This image was taken at an angle.
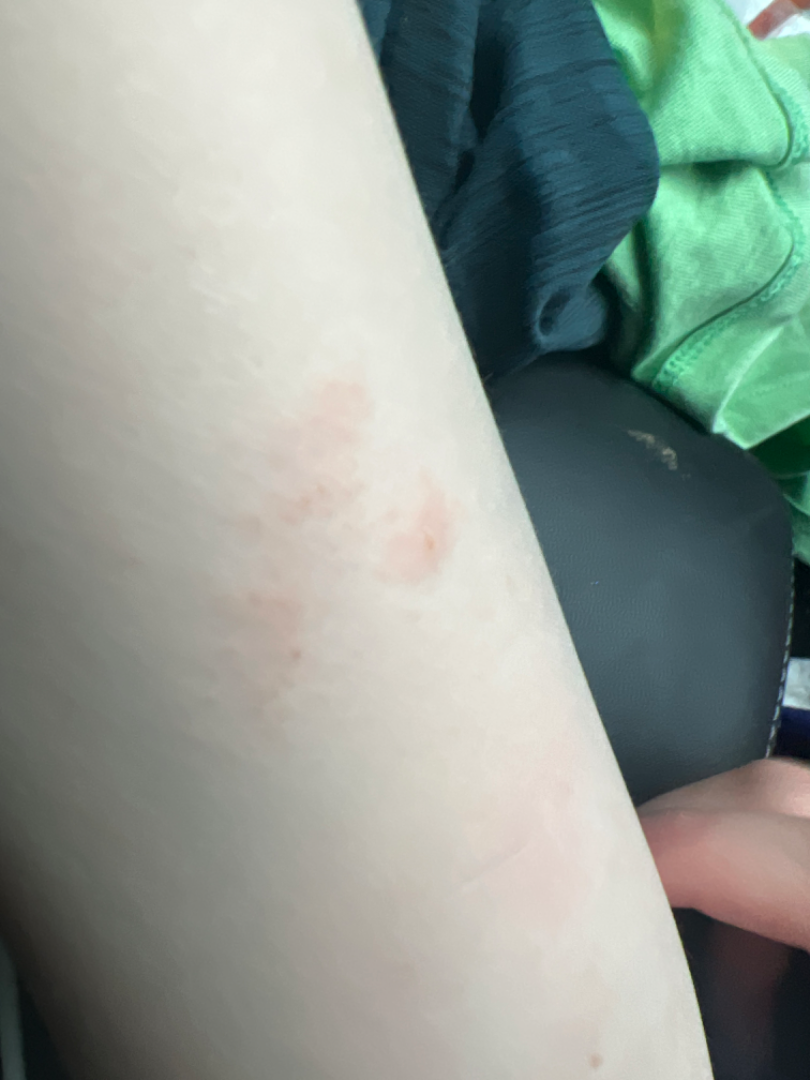No differential diagnosis could be assigned on photographic review.